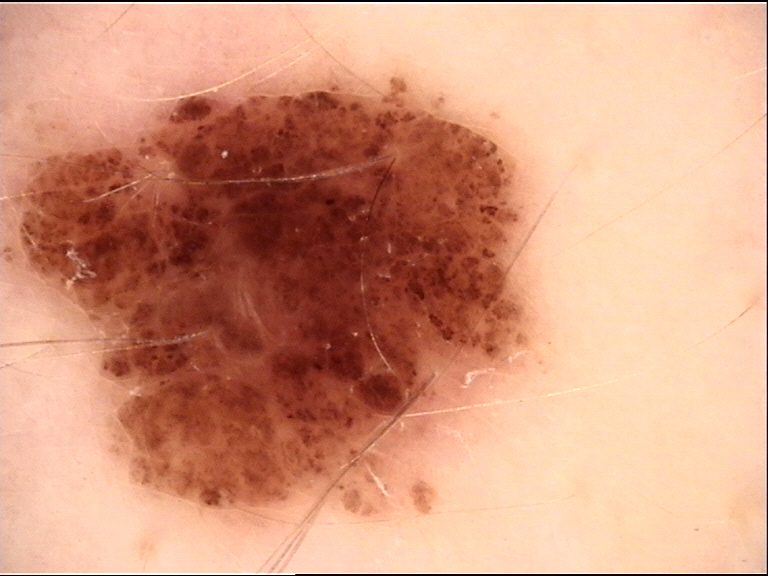A dermatoscopic image of a skin lesion.
Consistent with a compound nevus.